A skin lesion imaged with a dermatoscope.
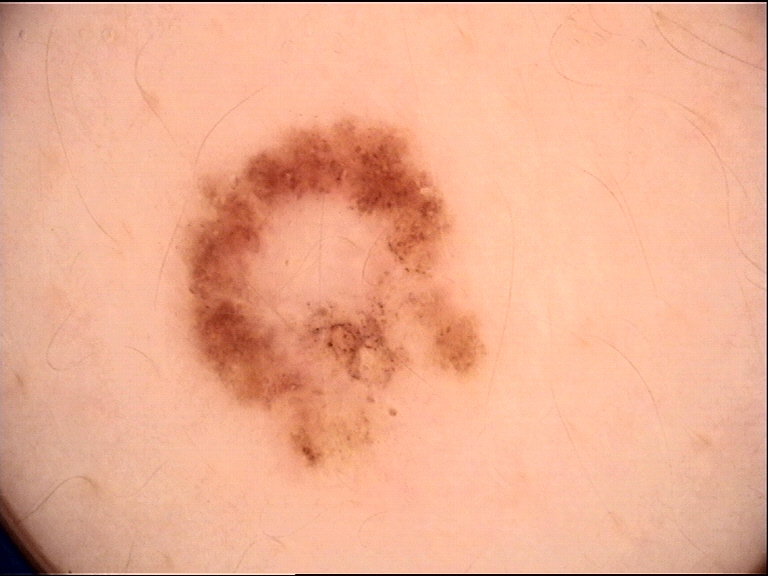Conclusion: Consistent with a dysplastic junctional nevus.